The leg is involved. This image was taken at a distance. The subject is 18–29, female. Symptoms reported: enlargement, bothersome appearance and itching.
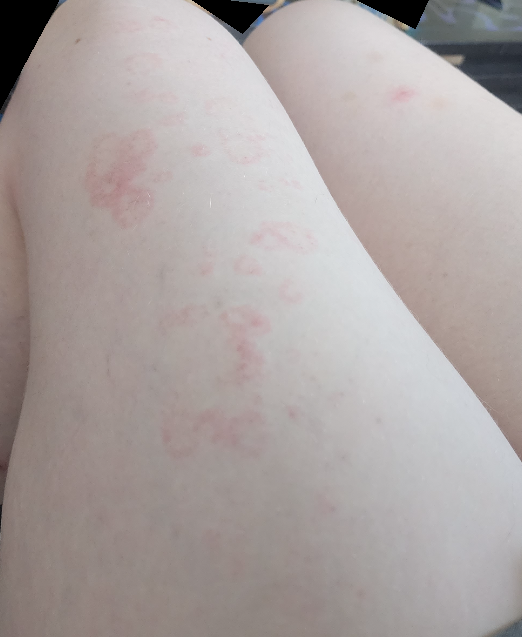The leading consideration is Urticaria; lower on the differential is Drug Rash; less likely is Erythema annulare centrifugum; less probable is Cutaneous lupus; a more distant consideration is Leukocytoclastic Vasculitis; a remote consideration is Cutaneous lyme disease.